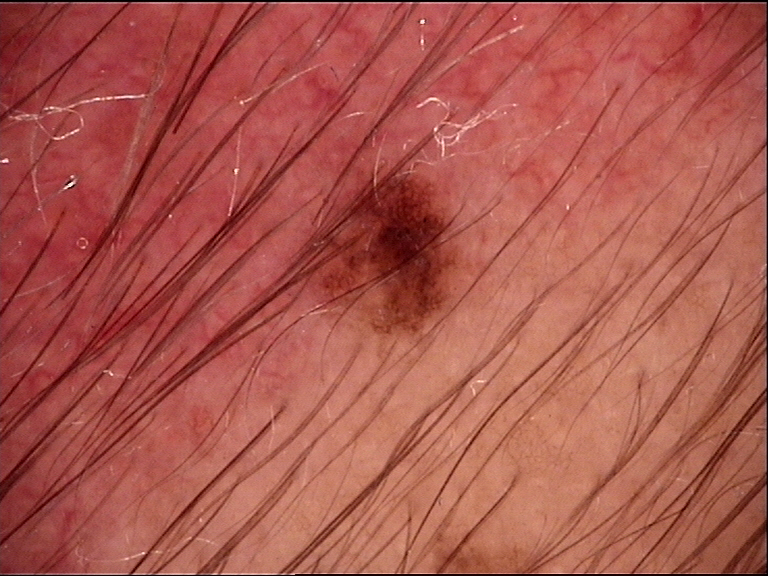The architecture is that of a banal lesion. The diagnostic label was a junctional nevus.